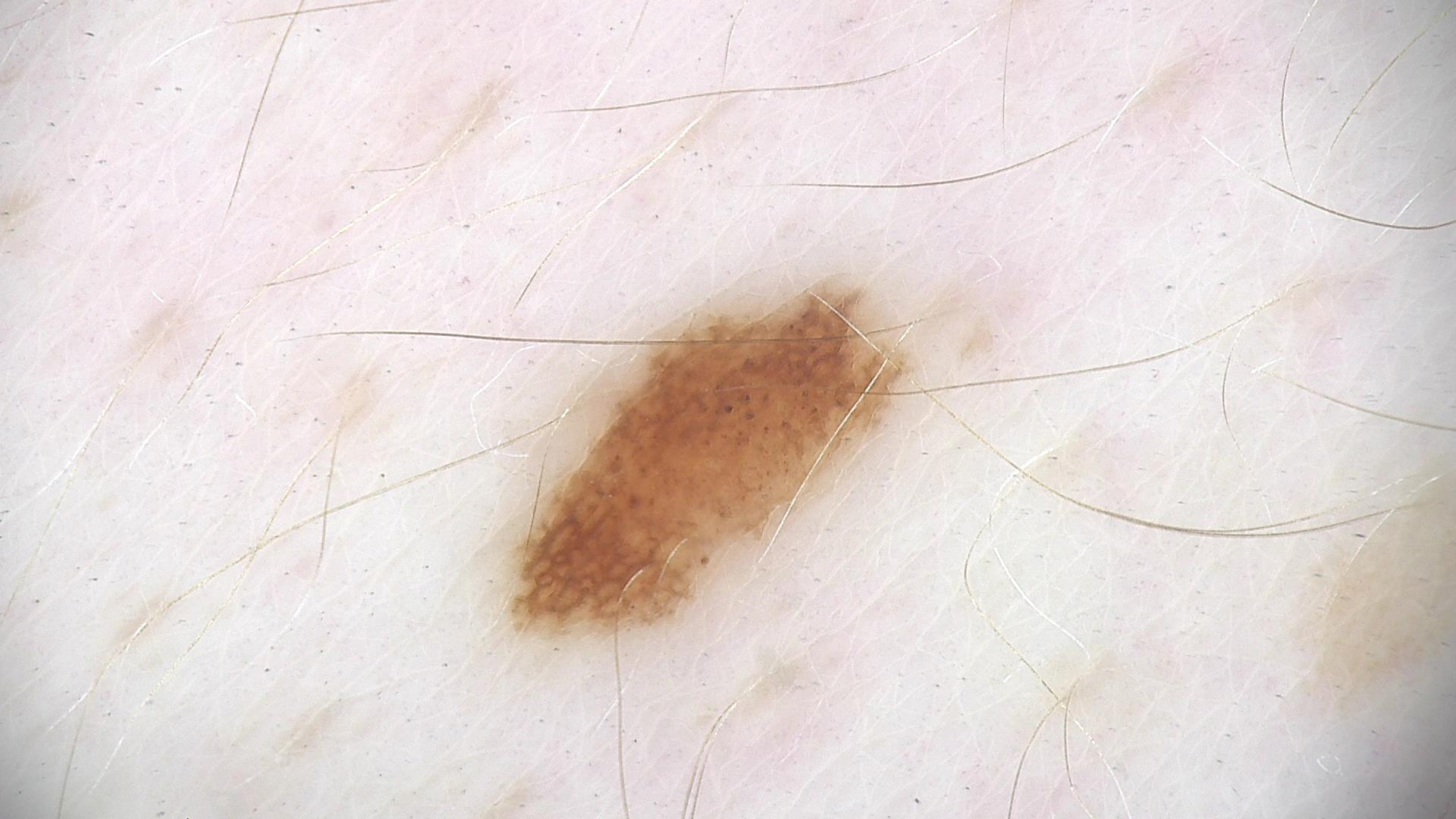diagnosis: dysplastic junctional nevus (expert consensus).